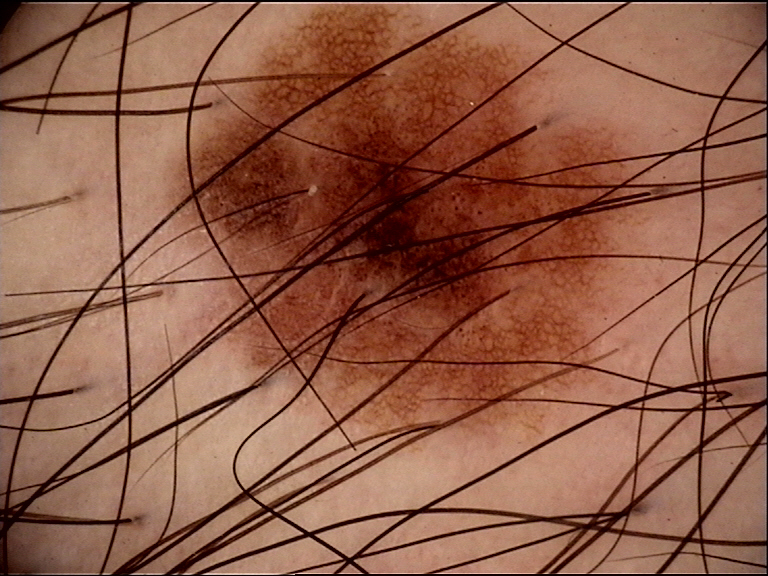Labeled as a dysplastic junctional nevus.